The lesion is associated with burning. Texture is reported as raised or bumpy. The lesion involves the back of the torso. The contributor is a female aged 18–29. A close-up photograph — 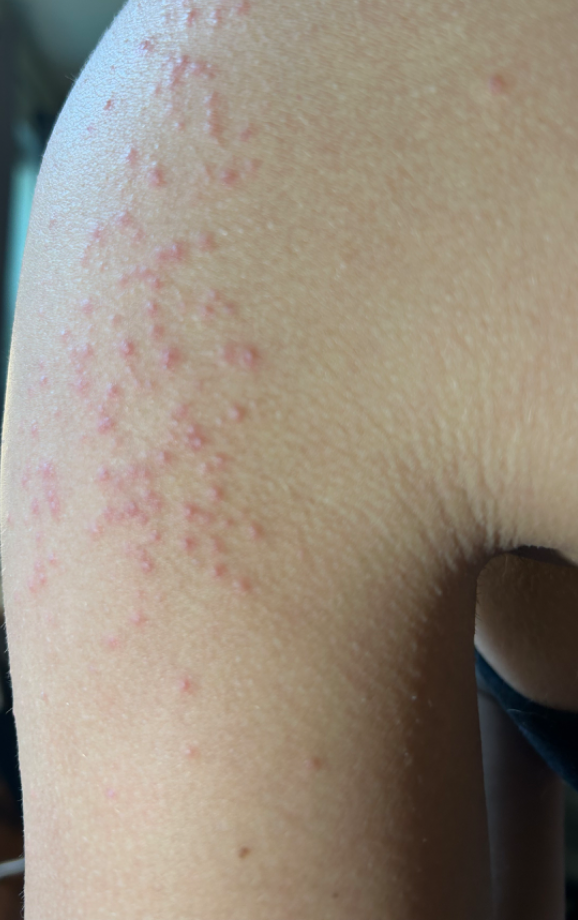Review:
The image was not sufficient for the reviewer to characterize the skin condition.